A dermoscopic photograph of a skin lesion.
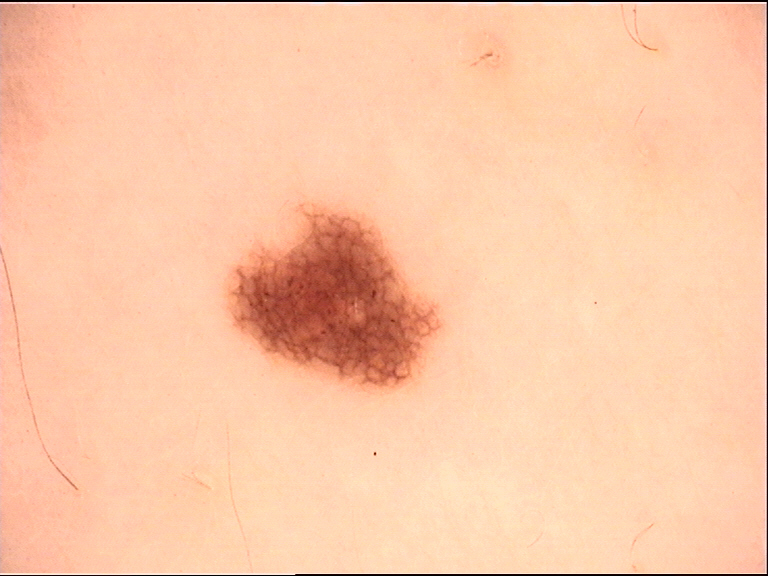Findings:
– class — dysplastic junctional nevus (expert consensus)